A smartphone photograph of a skin lesion. A female subject 77 years of age. The patient was assessed as FST II.
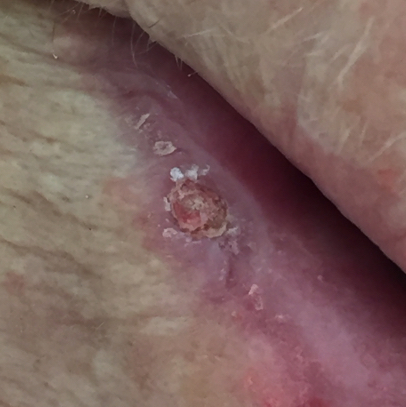anatomic site: a lip; symptoms: pain, elevation, itching / no bleeding, no growth; diagnosis: squamous cell carcinoma (biopsy-proven).